Referred for assessment of suspected basal cell carcinoma. Dermoscopy of a skin lesion. A female patient aged 84. The patient describes having few moles overall. On a questionnaire the patient reported a personal history of cancer. The patient says their skin tans without first burning.
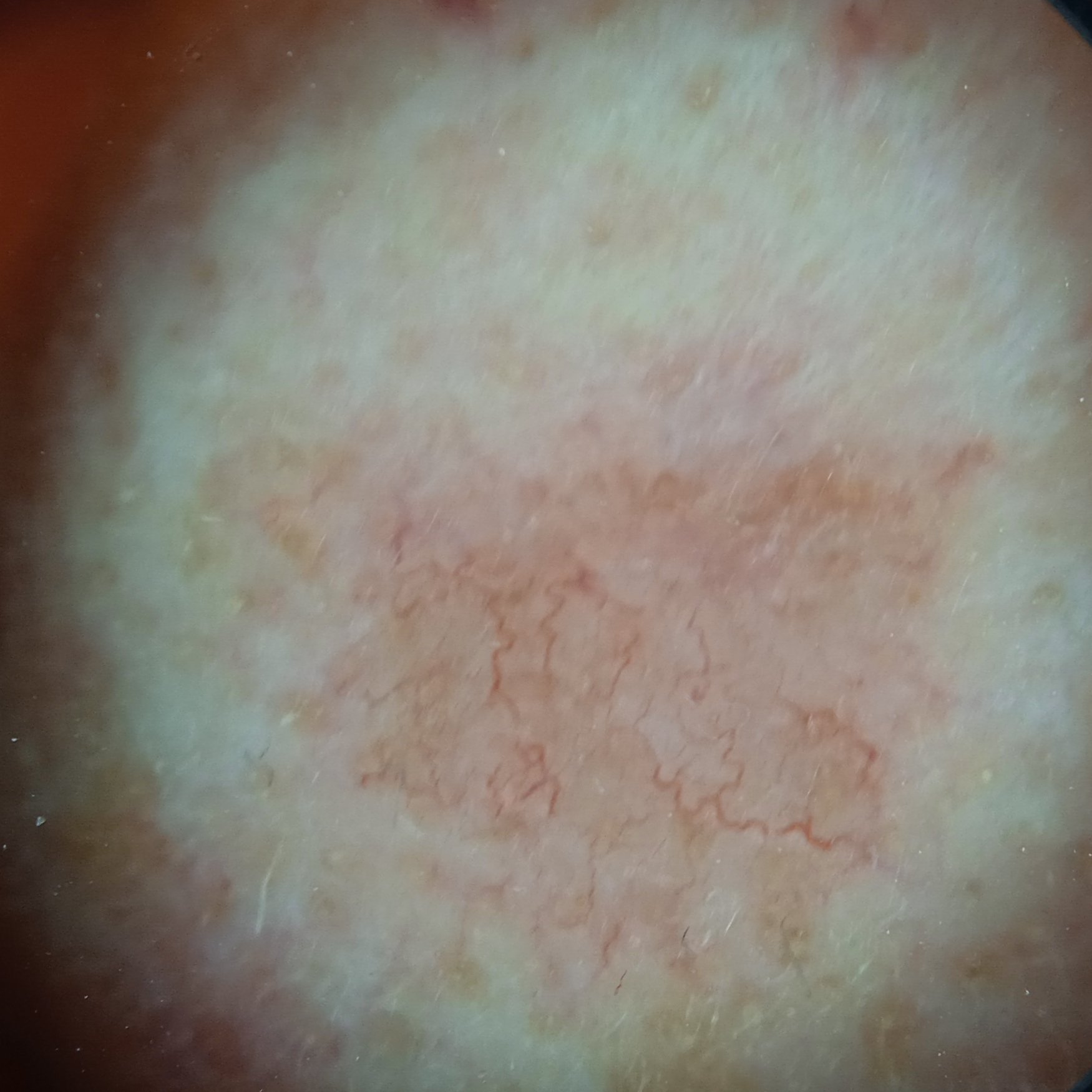Diagnosis:
Histopathology confirmed a basal cell carcinoma, following excision, with a measured tumor thickness of 1.5 mm.